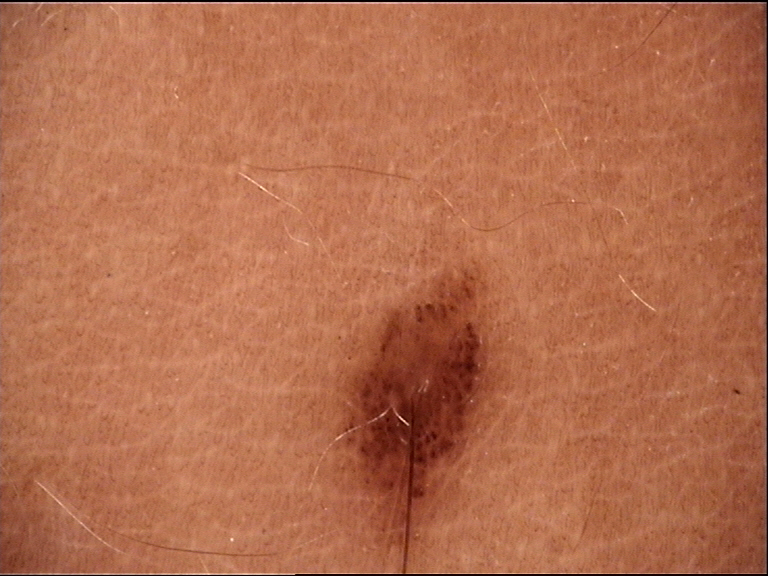diagnostic label — compound nevus (expert consensus).